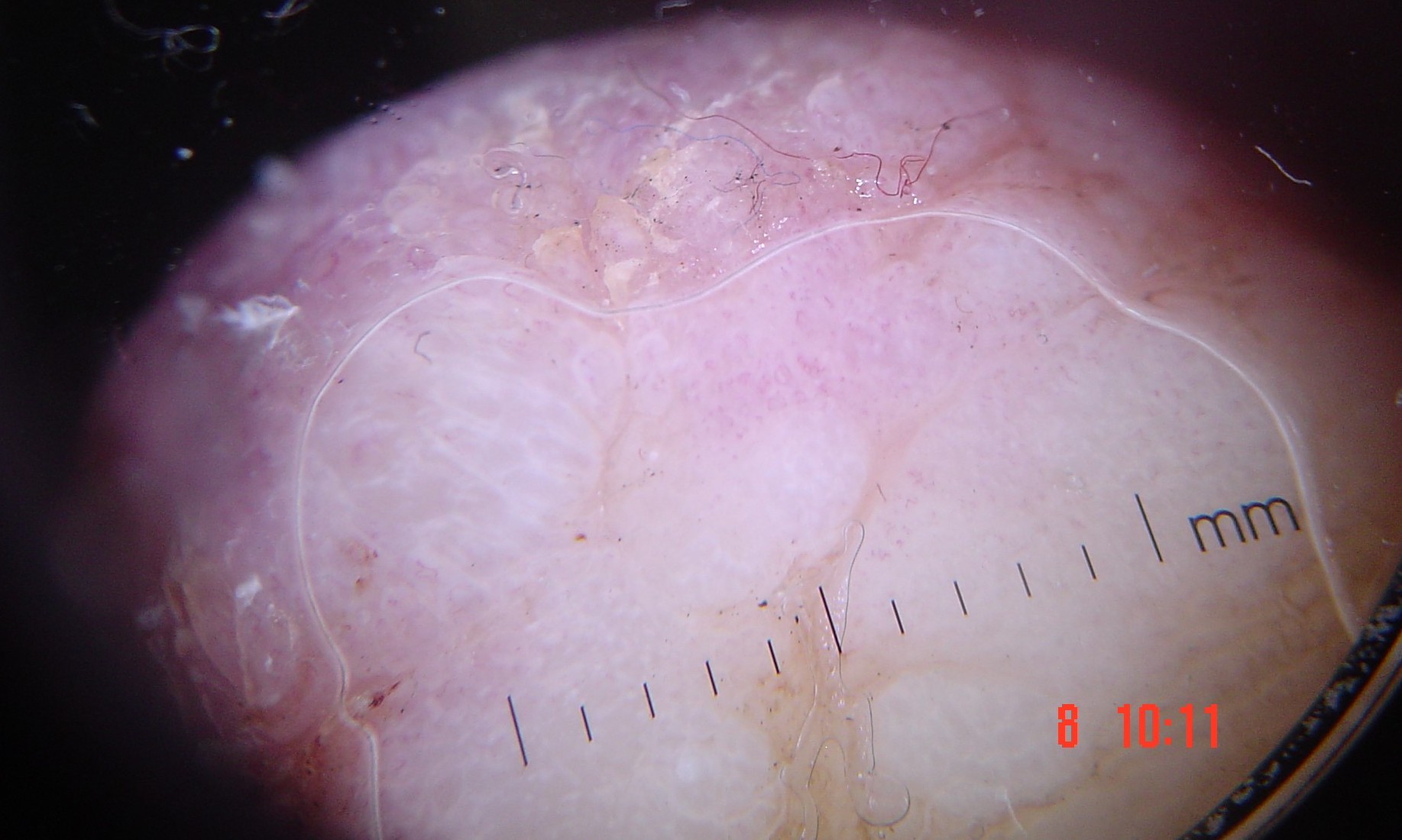image: dermatoscopy
diagnosis:
  name: acral nodular melanoma
  code: anm
  malignancy: malignant
  super_class: melanocytic
  confirmation: histopathology